Recorded as skin type I · a male subject in their mid-50s · a smartphone photograph of a skin lesion.
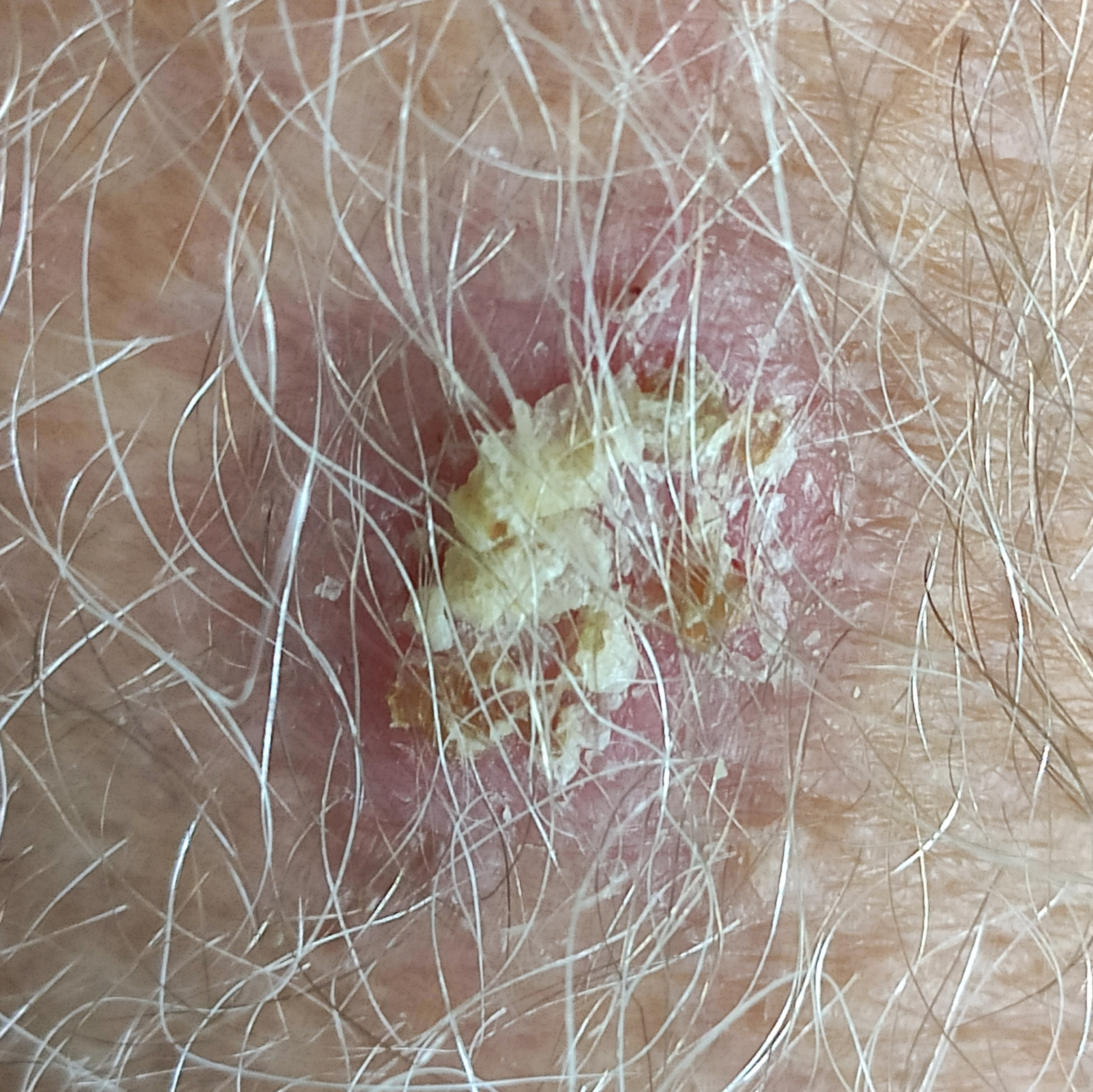diameter = approx. 20 × 15 mm
reported symptoms = change in appearance, elevation
pathology = basal cell carcinoma (biopsy-proven)